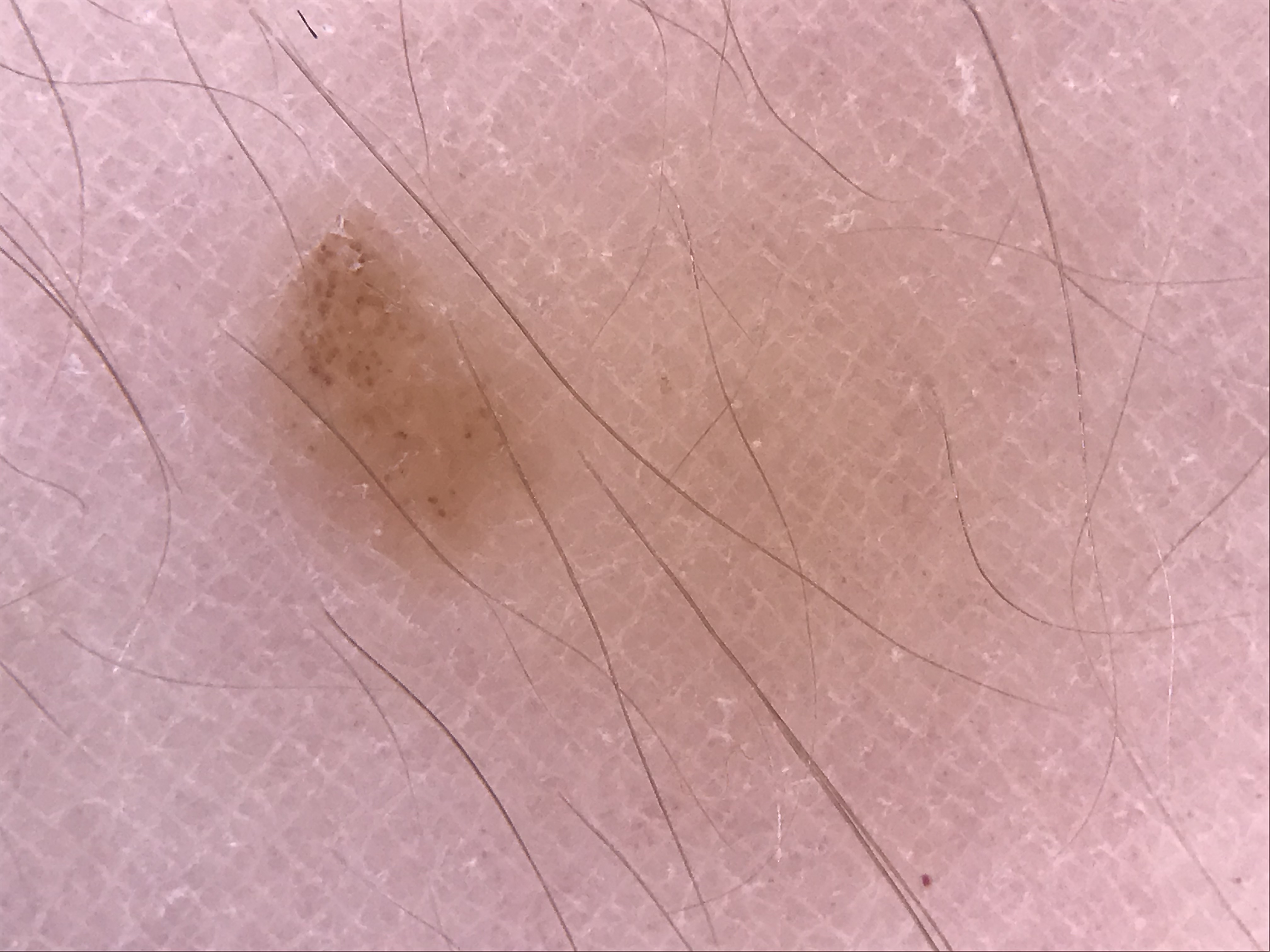<lesion>
  <diagnosis>
    <name>dysplastic junctional nevus</name>
    <code>jd</code>
    <malignancy>benign</malignancy>
    <super_class>melanocytic</super_class>
    <confirmation>expert consensus</confirmation>
  </diagnosis>
</lesion>